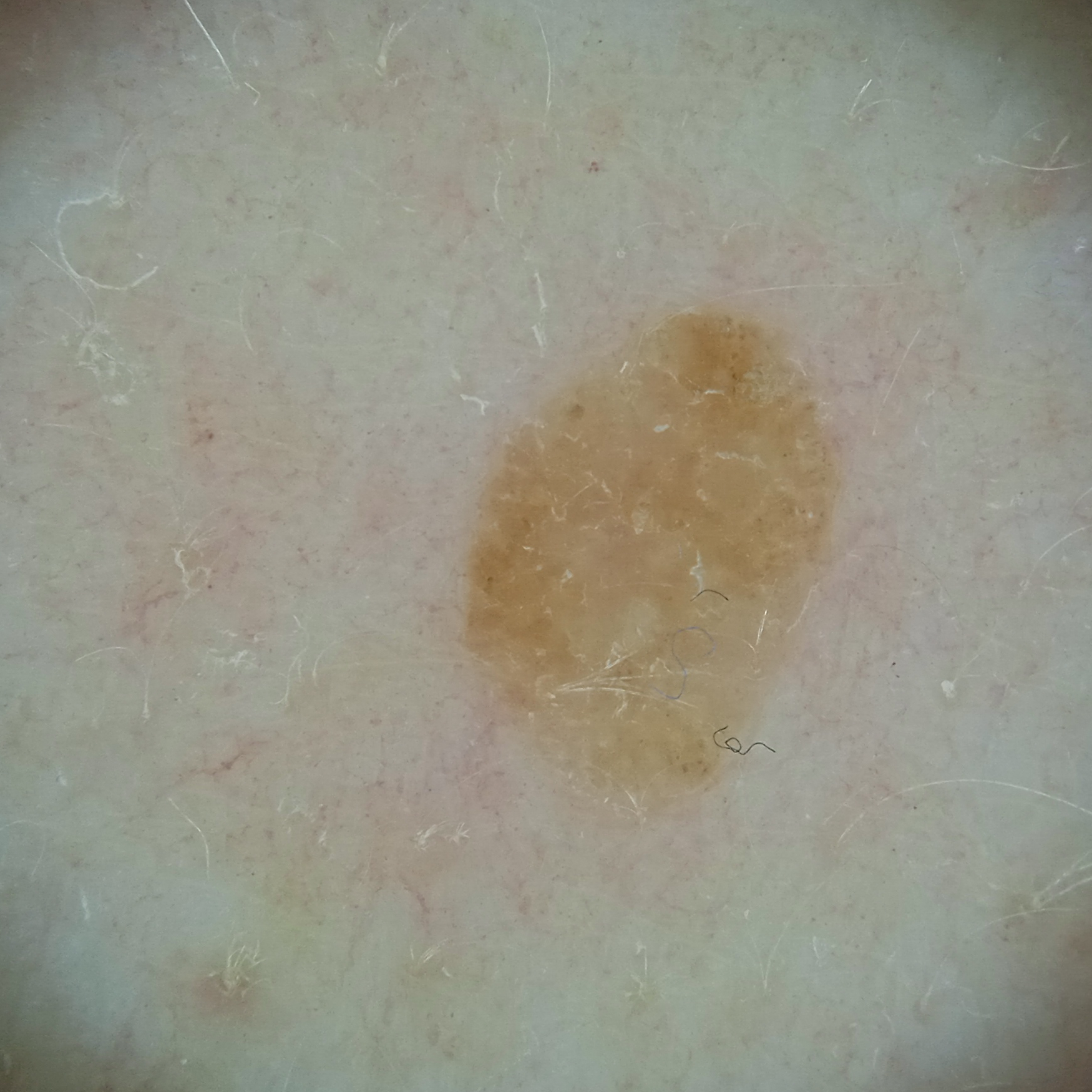Findings: A female patient age 54. Collected as part of a research study, without a referral diagnosis. The patient says their skin reddens with sun exposure. The patient reports a personal history of cancer, a family history of skin cancer, a personal history of skin cancer, and no sunbed use. A dermoscopy image of a skin lesion. The patient describes having numerous moles. Located on the back. The lesion measures approximately 5.5 mm. Assessment: The diagnostic impression was a seborrheic keratosis.